A close-up photograph: 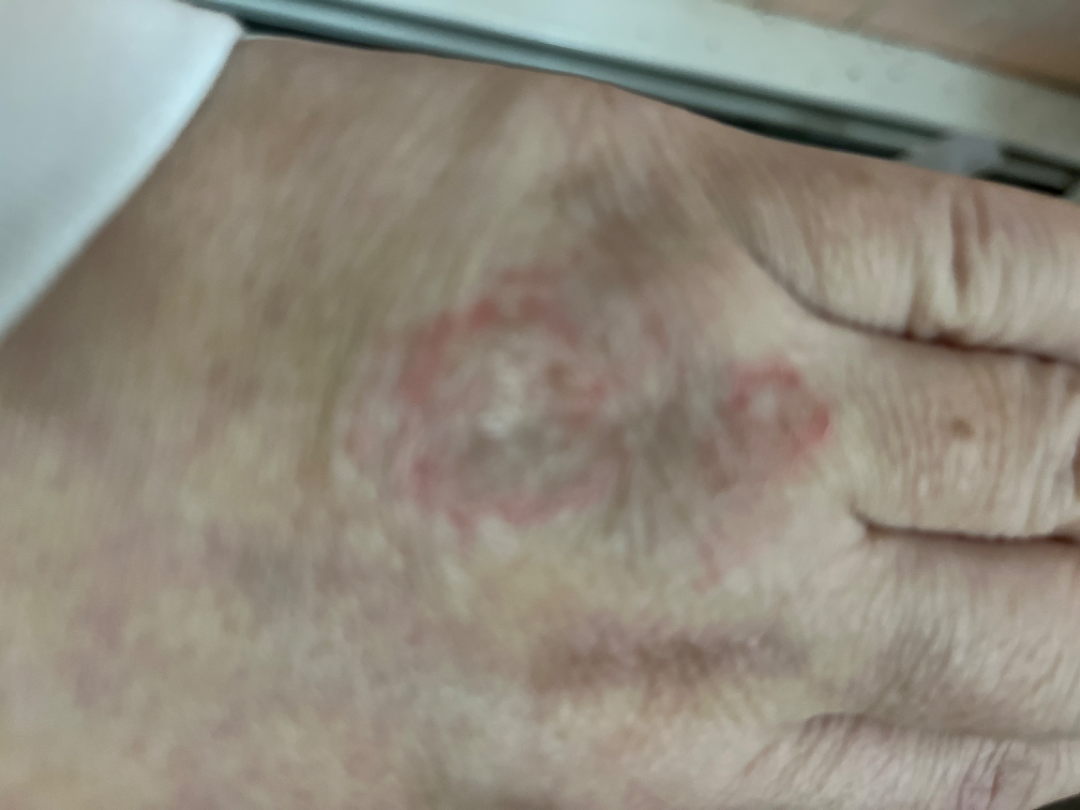Tinea and Eczema were considered with similar weight.